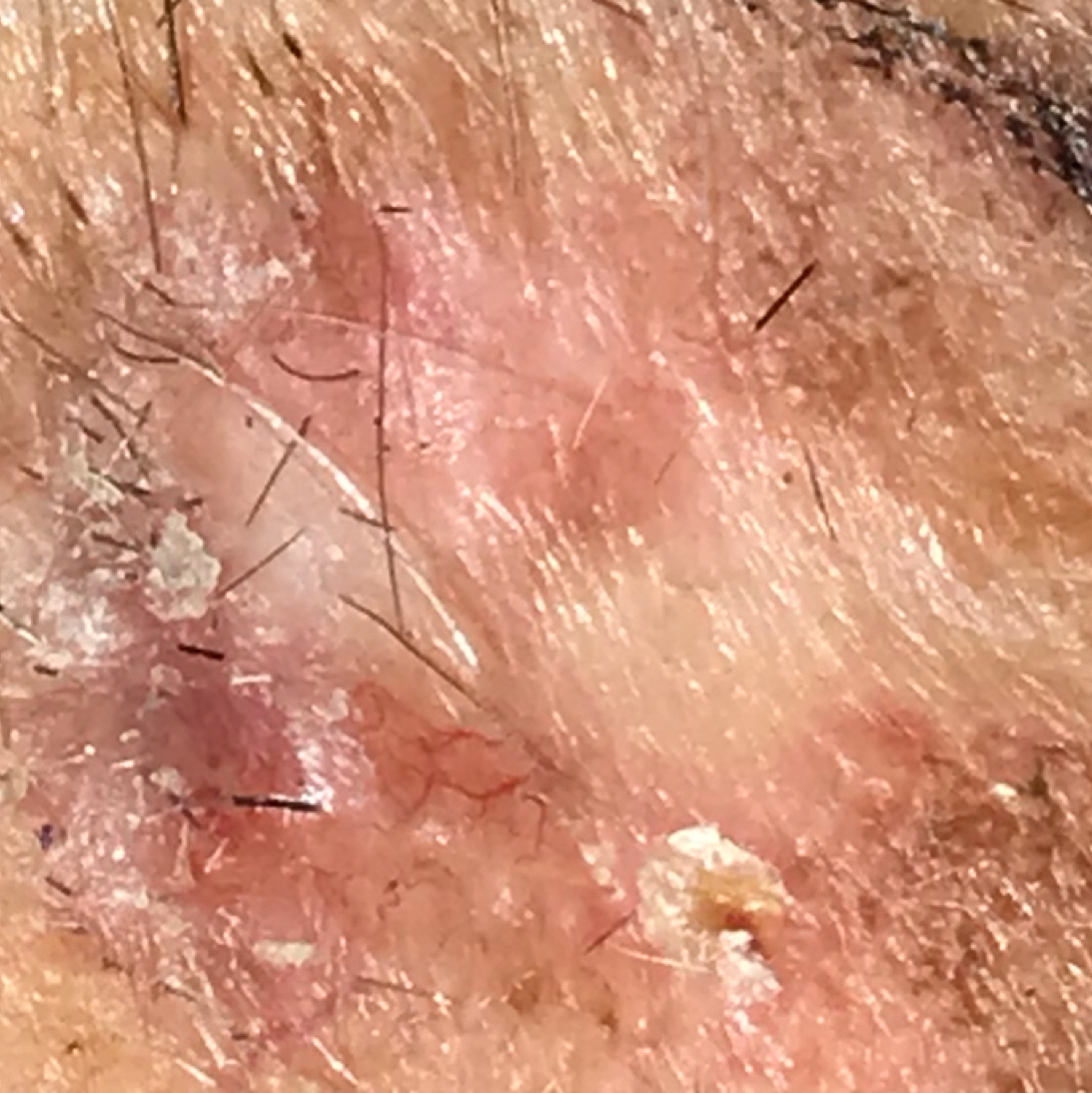Summary: The patient is Fitzpatrick phototype II. By history, alcohol use, no prior malignancy (patient or family), and no tobacco use. A male subject 61 years of age. A clinical photograph of a skin lesion. The lesion involves the face. The lesion measures 10 × 9 mm. Conclusion: On biopsy, the diagnosis was a basal cell carcinoma.